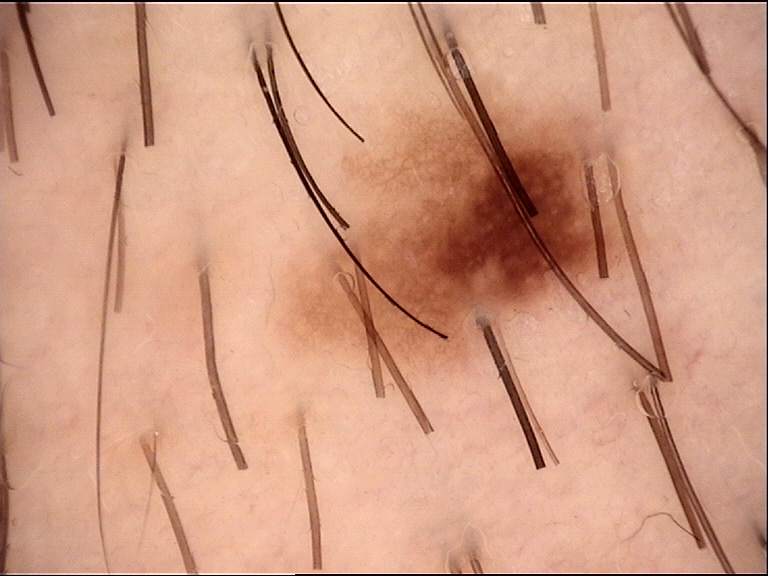Classified as a benign lesion — a dysplastic junctional nevus.